The photograph is a close-up of the affected area; the affected area is the leg; the contributor is 60–69, male: 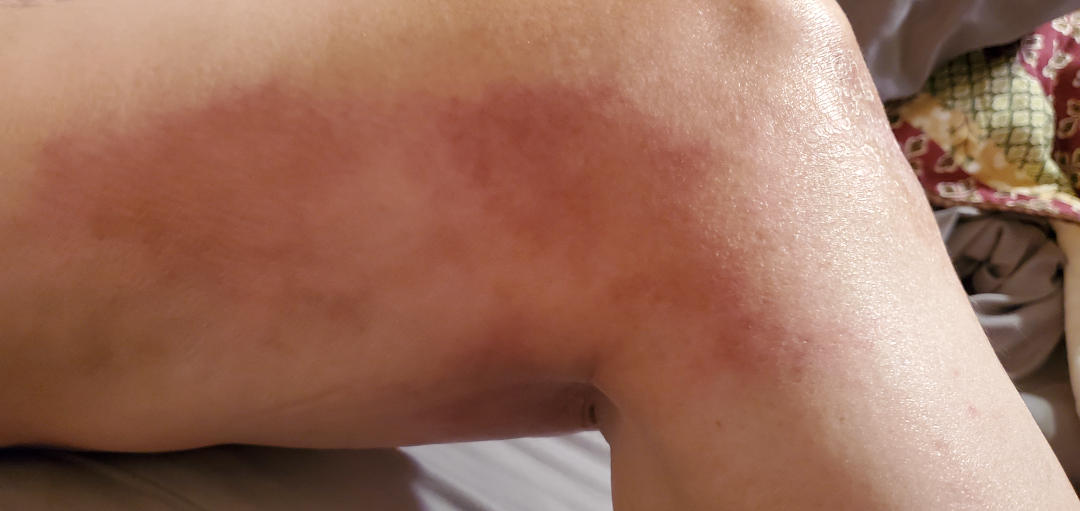Assessment: The condition could not be reliably identified from the image. Clinical context: The contributor reports bothersome appearance. The condition has been present for about one day. The patient described the issue as a rash.